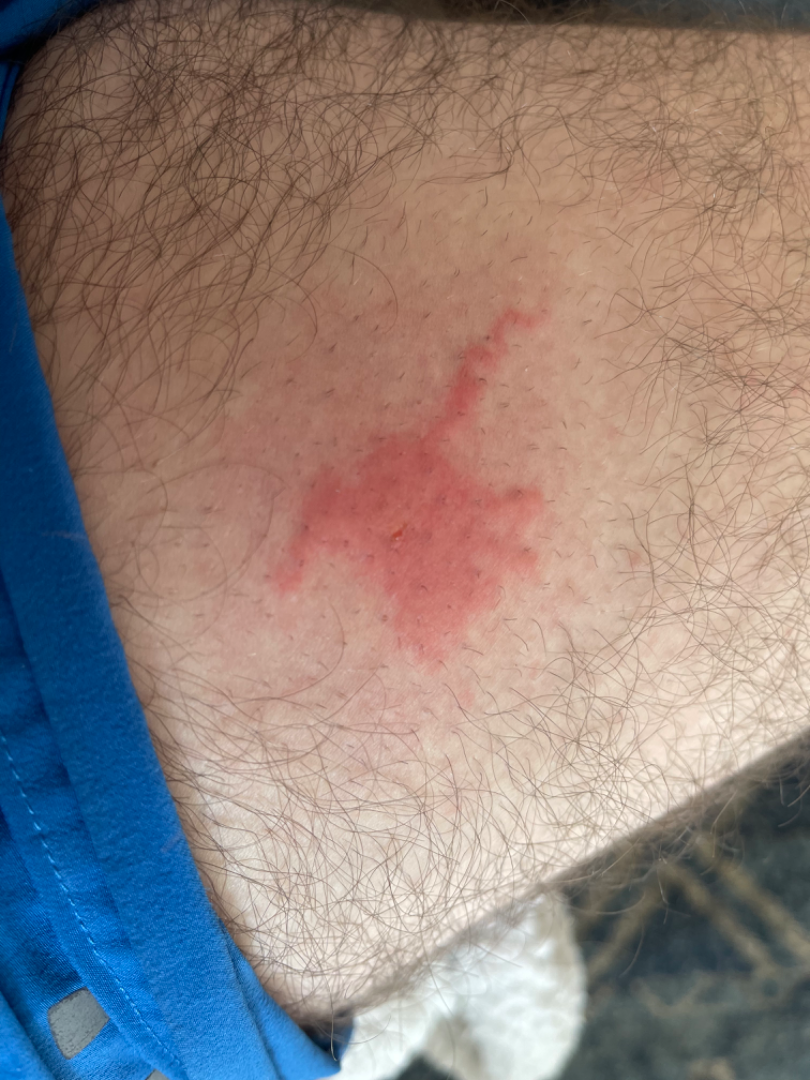Self-categorized by the patient as a rash. Male contributor, age 30–39. Reported duration is less than one week. The patient reported no systemic symptoms. Texture is reported as raised or bumpy. The lesion involves the leg. This is a close-up image. The lesion is associated with itching. A single dermatologist reviewed the case: the primary impression is Poisoning by nematocyst; also consider Cutaneous larva migrans.